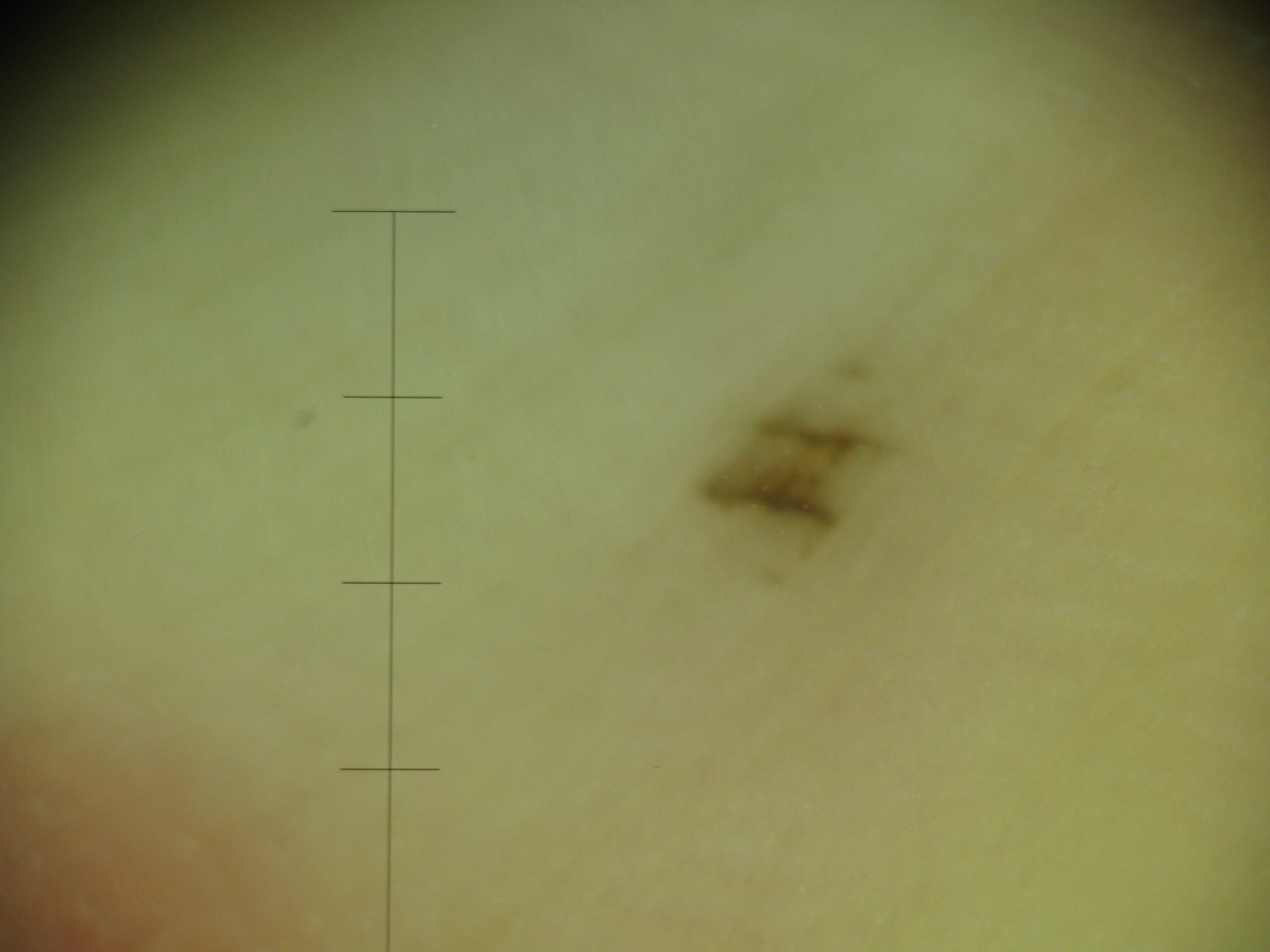Impression: The diagnostic label was an acral junctional nevus.